The photograph is a close-up of the affected area — 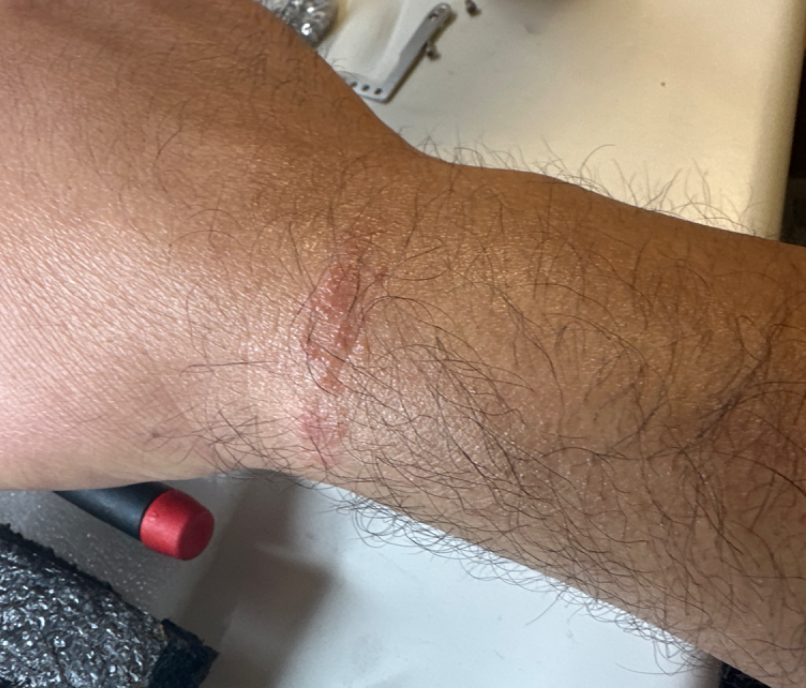diagnostic considerations = the differential is split between Scar Condition; Allergic Contact Dermatitis; and Abrasion, scrape, or scab.